The patient was assessed as Fitzpatrick III. By history, alcohol use. A clinical photo of a skin lesion taken with a smartphone: 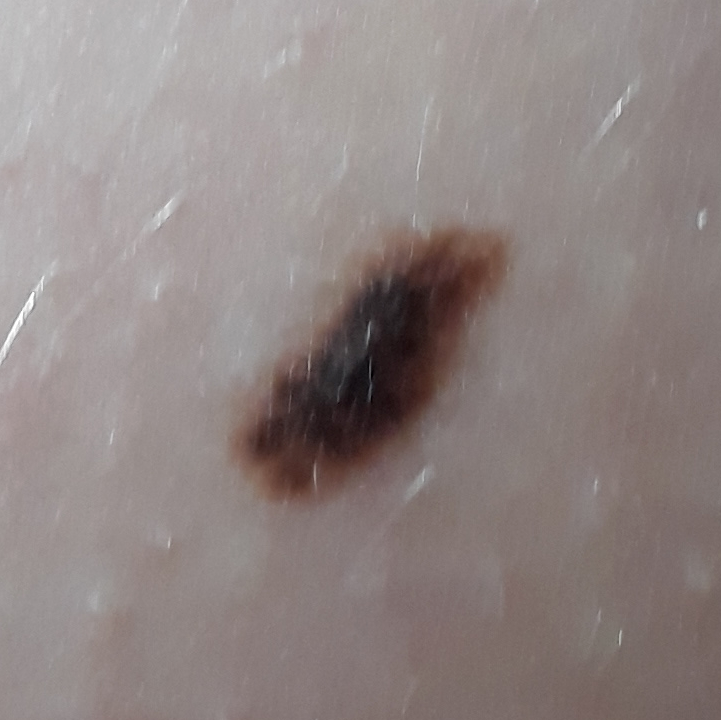Findings:
* location — a thigh
* lesion size — approx. 8 × 3 mm
* reported symptoms — no itching
* diagnosis — nevus (biopsy-proven)